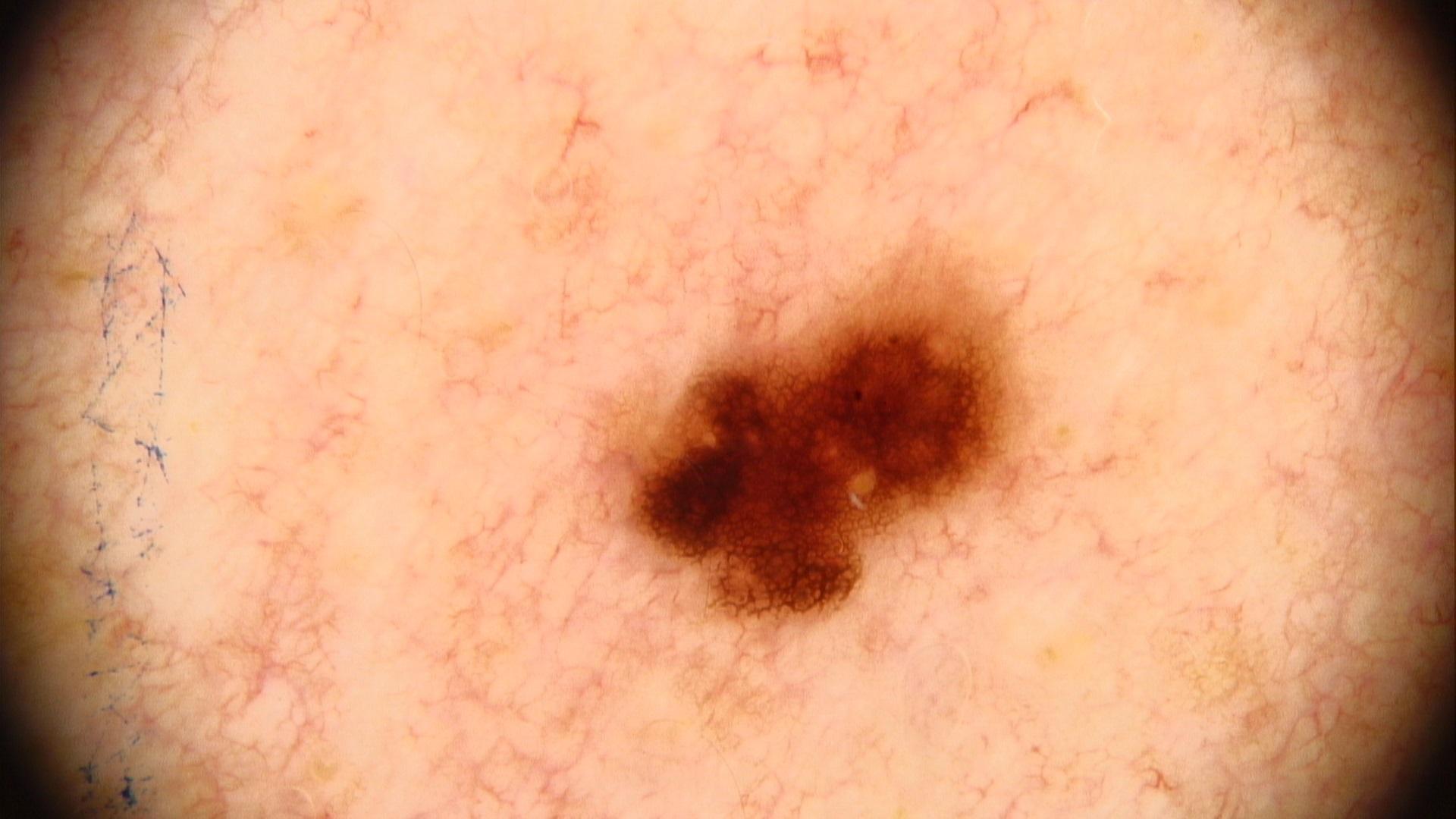image type — contact-polarized dermoscopy
patient — male, in their mid-40s
location — the trunk
pathology — Nevus (biopsy-proven)